This is a dermoscopic photograph of a skin lesion — 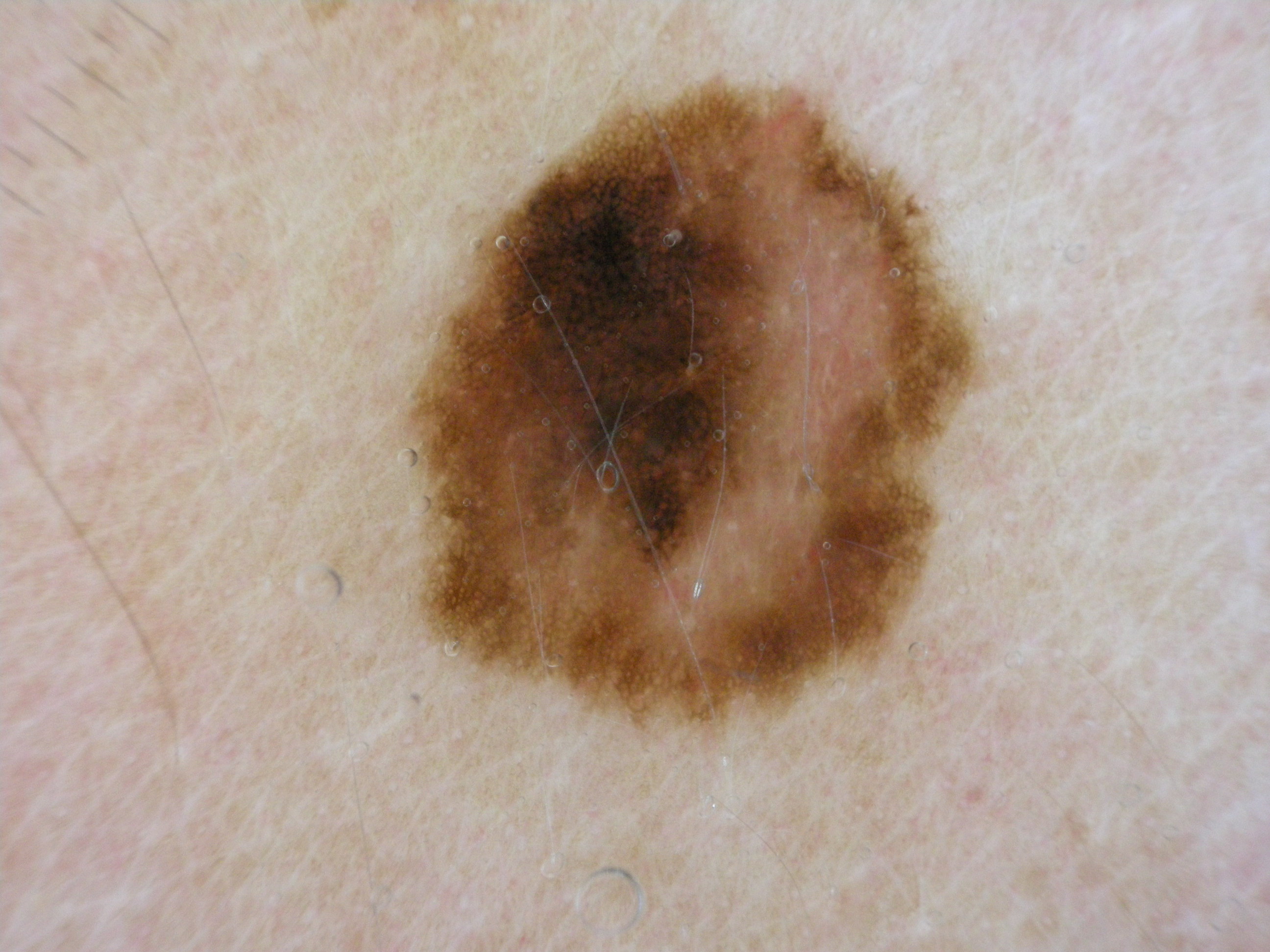The lesion occupies roughly 23% of the field. Dermoscopic assessment notes negative network, milia-like cysts, and pigment network, with no streaks or globules. The lesion is bounded by bbox=[405, 85, 978, 737]. Confirmed on histopathology as a melanoma, a malignant lesion.